A dermatoscopic image of a skin lesion.
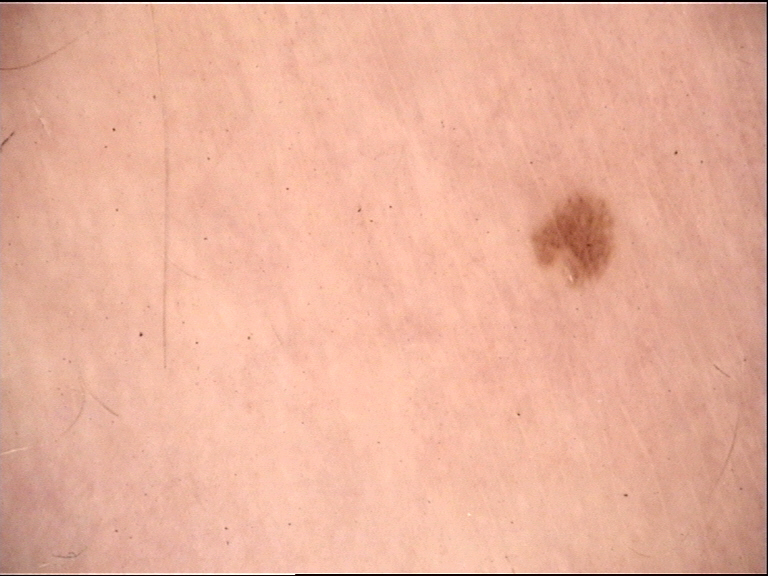The architecture is that of a banal lesion.
Classified as a junctional nevus.